A dermatoscopic image of a skin lesion: 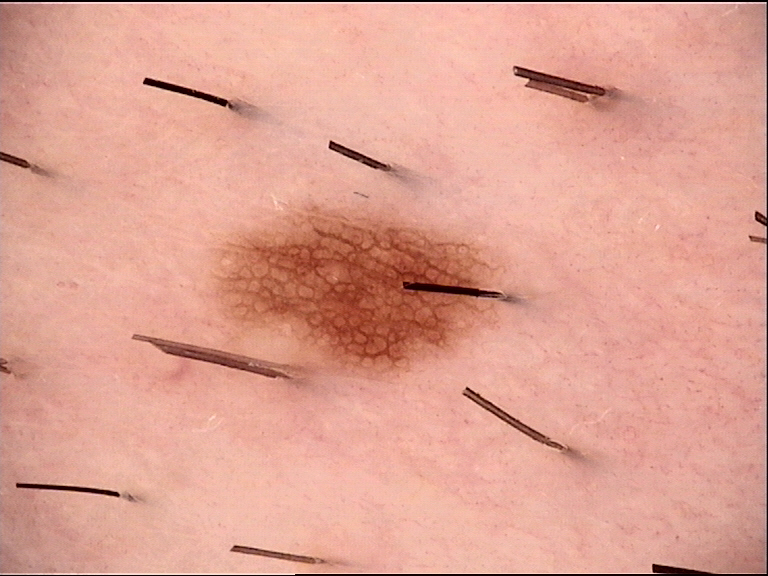Consistent with a benign lesion — a dysplastic junctional nevus.